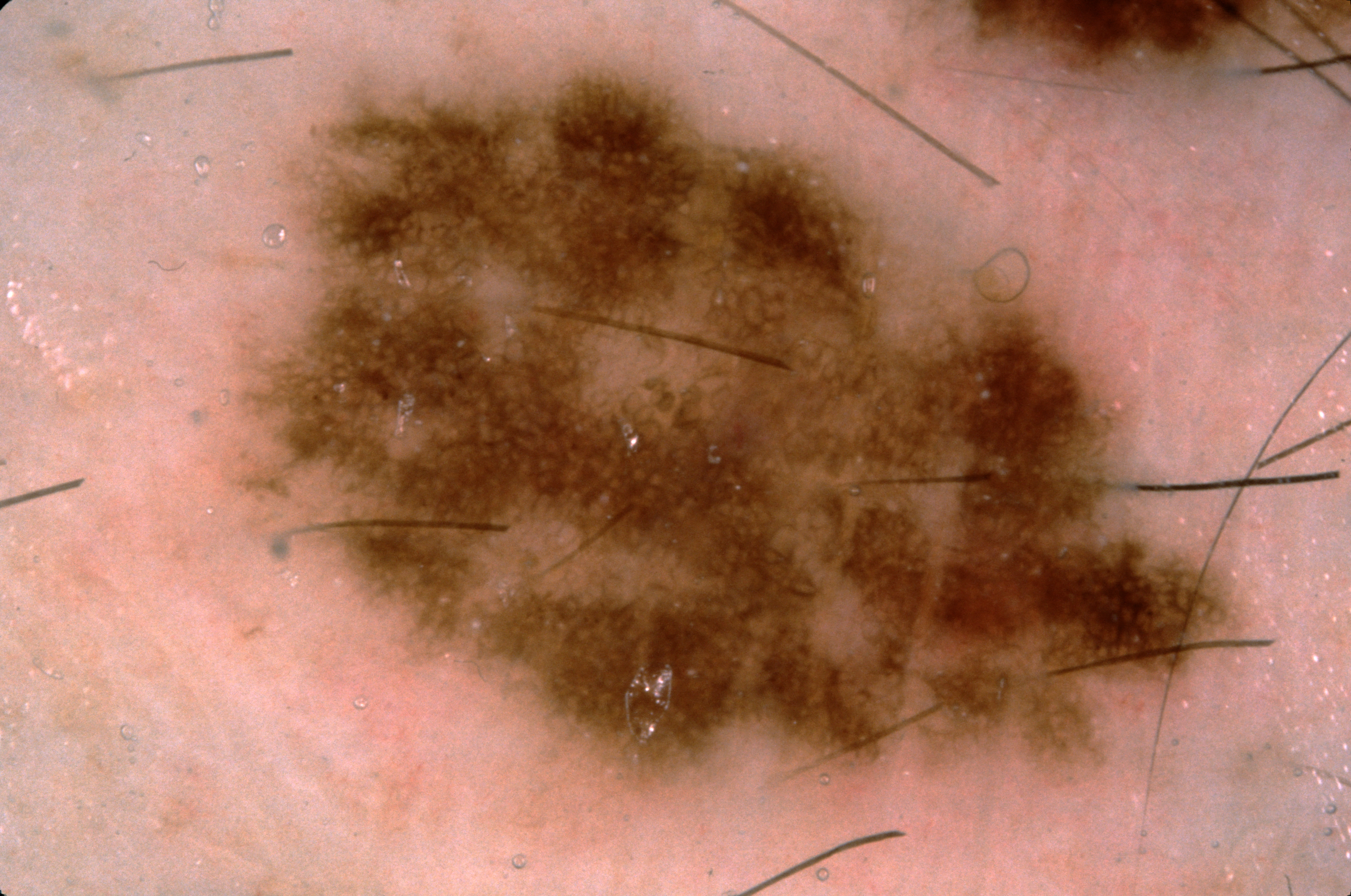Notes:
– image type · dermoscopy of a skin lesion
– dermoscopic features · pigment network; absent: streaks, negative network, and milia-like cysts
– lesion margin · extends past the field edge
– lesion location · 236/51/1350/798
– lesion size · ~43% of the field
– diagnosis · a melanocytic nevus